A dermoscopic close-up of a skin lesion: 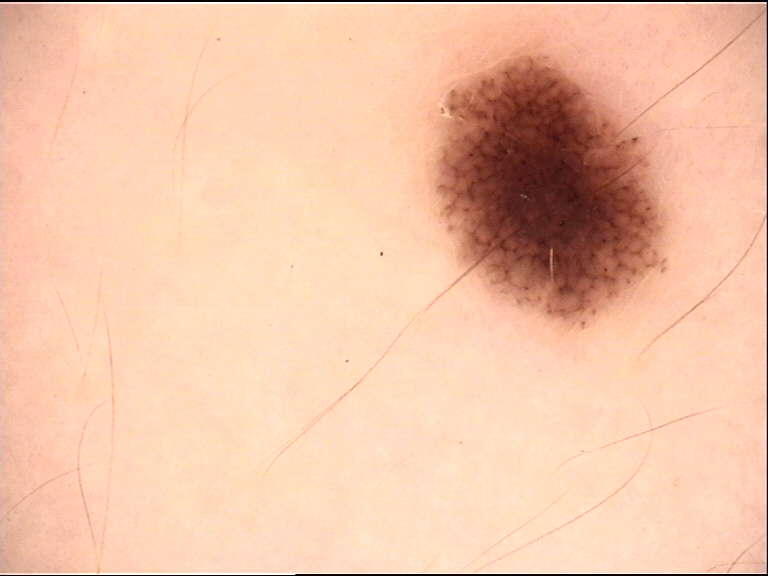Diagnosed as a benign lesion — a dysplastic junctional nevus.